Collected as part of a research study, without a referral diagnosis. A clinical photograph showing a skin lesion. A male patient 76 years of age: 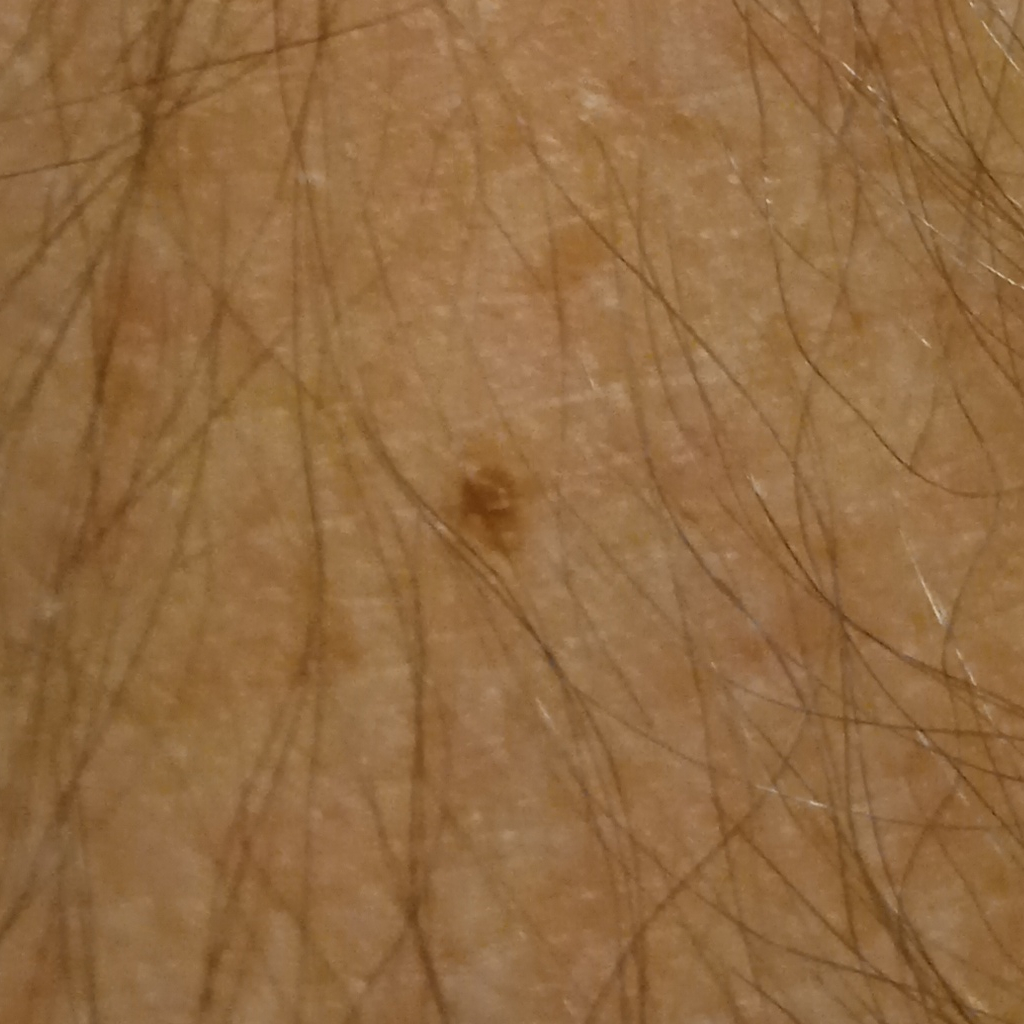Located on an arm. Measuring roughly 8.2 mm. The lesion was assessed as a melanocytic nevus.